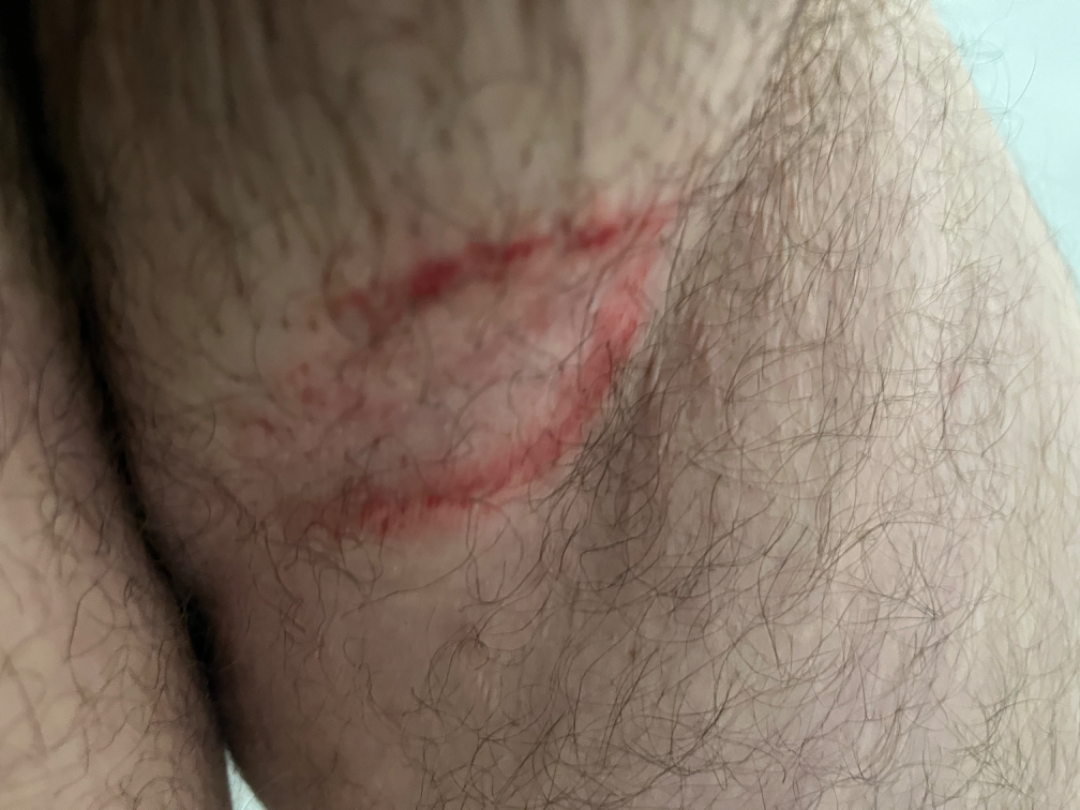- diagnostic considerations · favoring Intertrigo; possibly Skin infection; the differential also includes Psoriasis